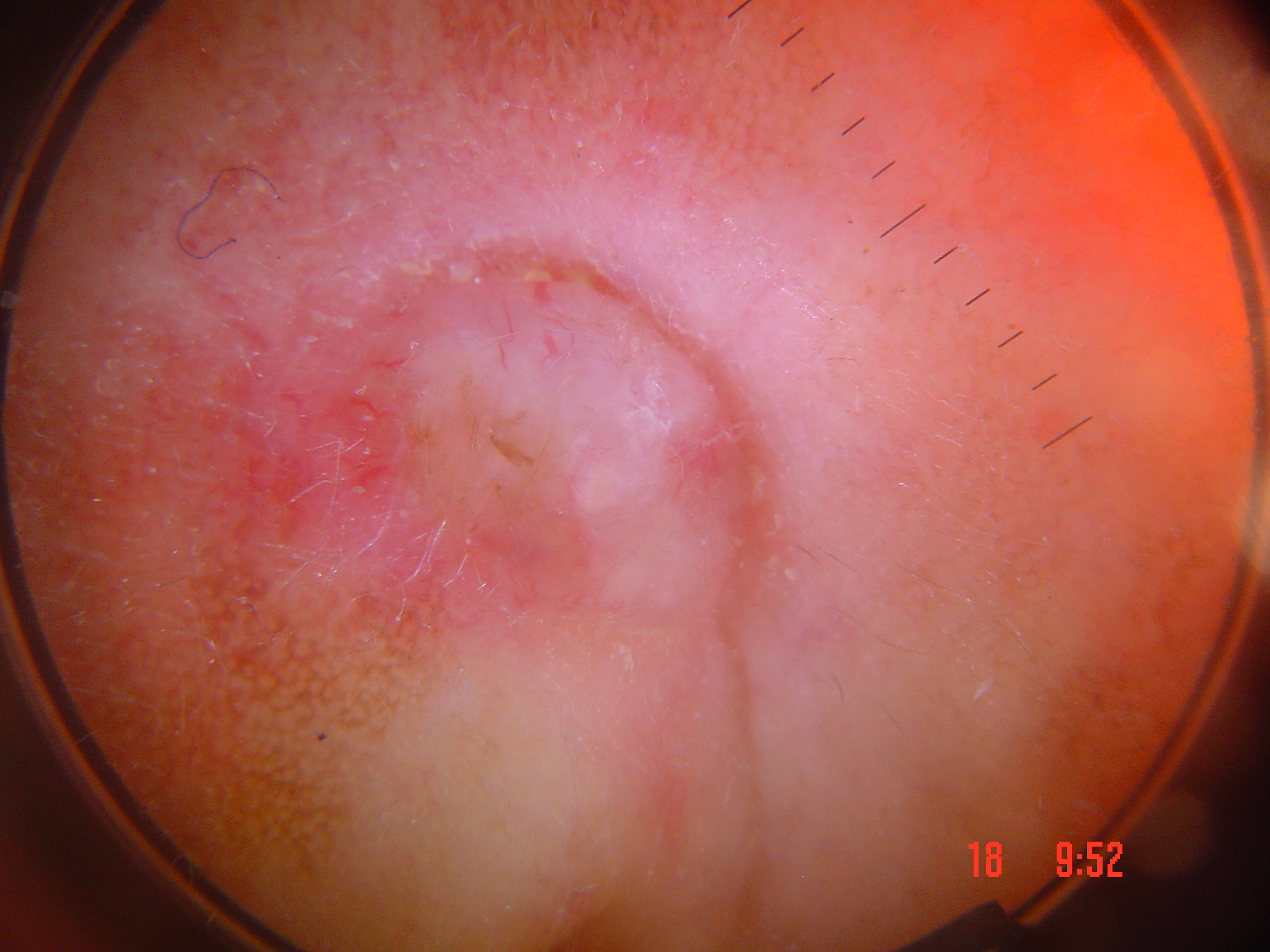<case>
<image>dermoscopy</image>
<lesion_type>
<main_class>keratinocytic</main_class>
</lesion_type>
<diagnosis>
<name>basal cell carcinoma</name>
<code>bcc</code>
<malignancy>malignant</malignancy>
<super_class>non-melanocytic</super_class>
<confirmation>histopathology</confirmation>
</diagnosis>
</case>